A female subject age 48; acquired for a research image collection, with no referral diagnosis; a dermatoscopic image of a skin lesion; the patient describes having few moles overall; the patient says their skin reddens painfully with sun exposure; by self-report, a family history of skin cancer and a history of sunbed use:
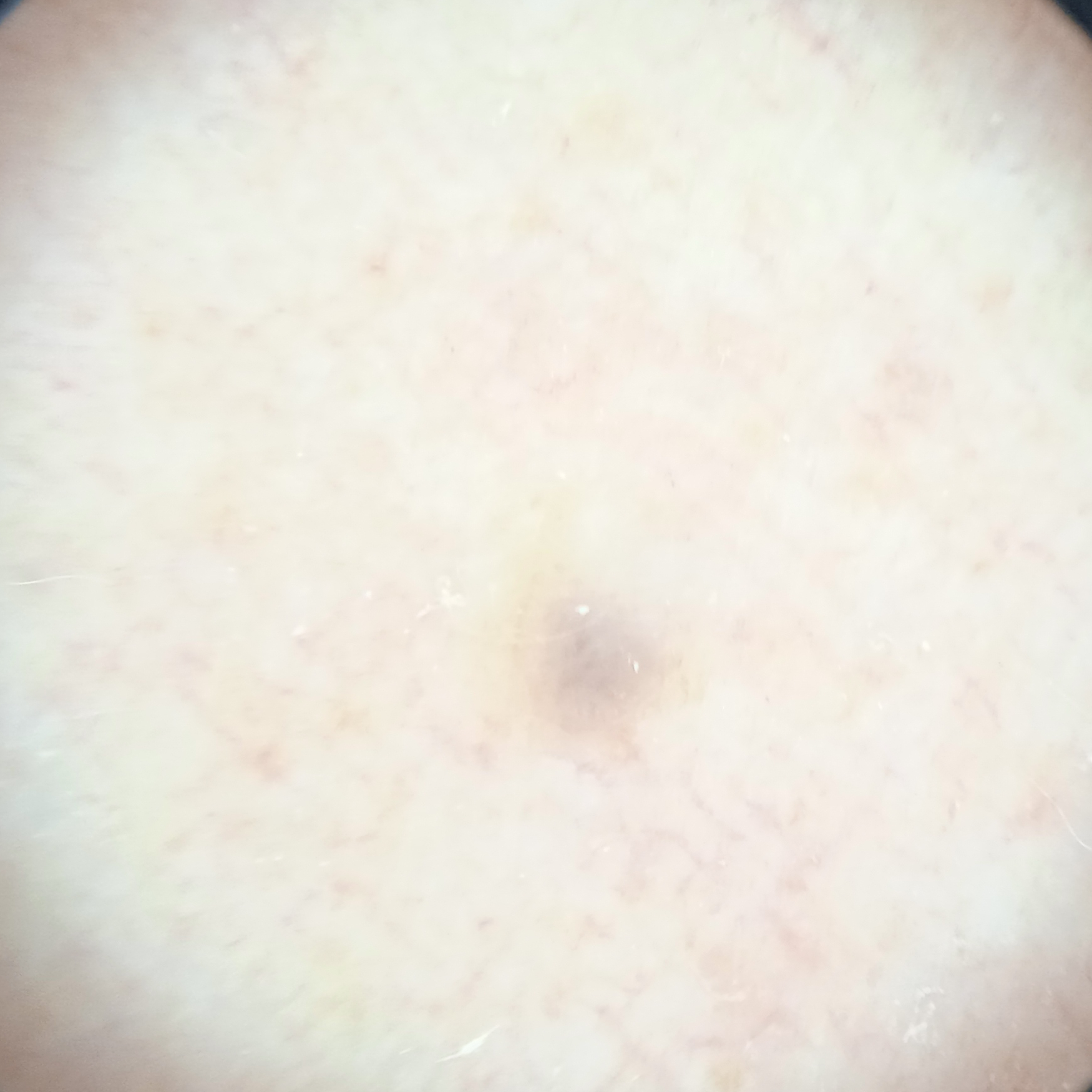site: an arm; diameter: 1.8 mm; diagnostic label: melanocytic nevus (dermatologist consensus).